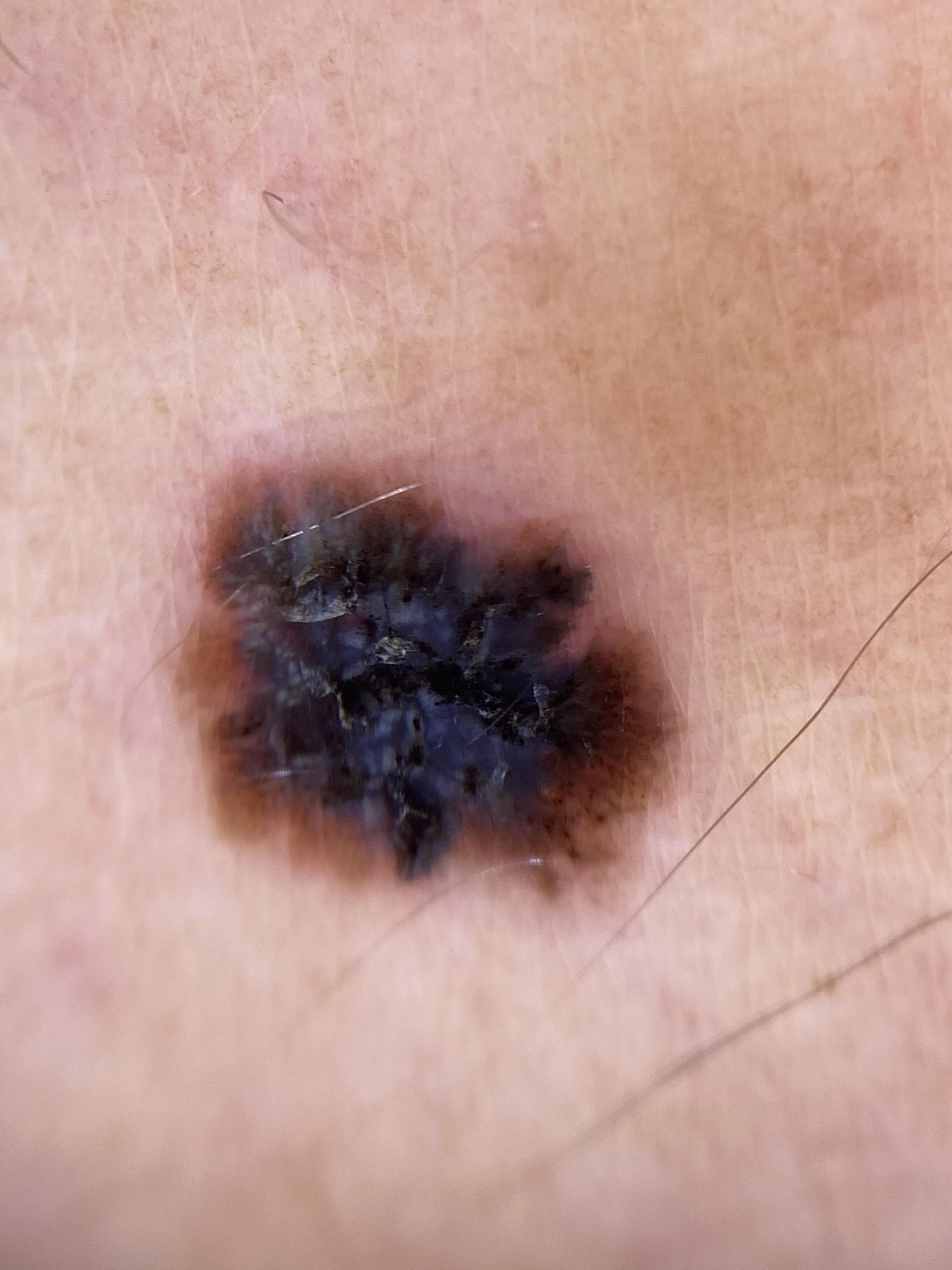patient: female, roughly 45 years of age; melanoma history: a prior melanoma; image: contact-polarized dermoscopy; anatomic site: an upper extremity; diagnosis: Melanoma (biopsy-proven).